A male subject aged 68-72. The patient was assessed as FST II. A dermoscopic image of a skin lesion. The chart documents a previous melanoma but no first-degree relative with melanoma — 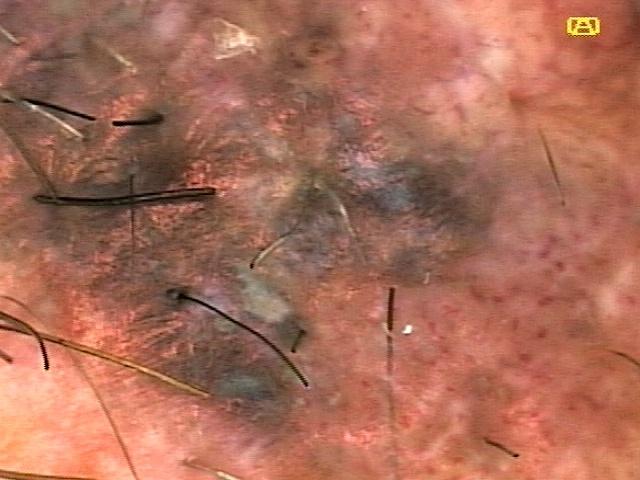Q: What is the anatomic site?
A: an upper extremity
Q: What did the workup show?
A: Melanoma (biopsy-proven)